The affected area is the leg. The photograph is a close-up of the affected area.
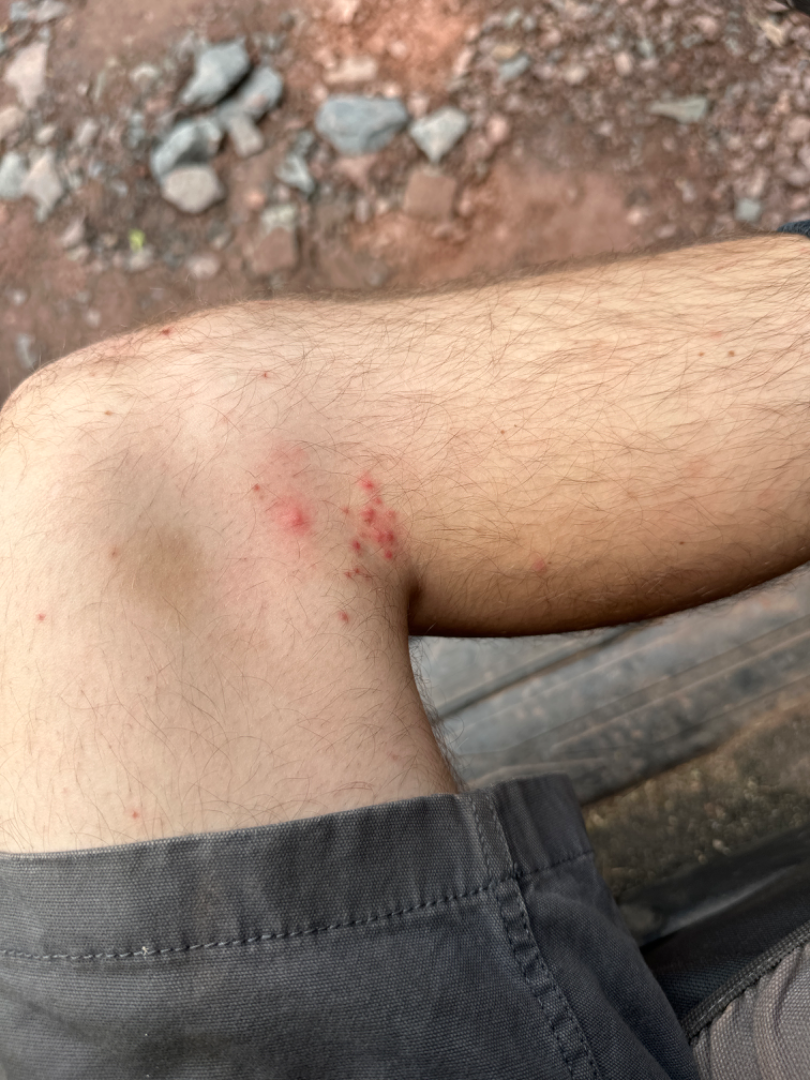Q: Could the case be diagnosed?
A: not assessable
Q: What is the lesion texture?
A: raised or bumpy
Q: How does the patient describe it?
A: a rash
Q: Duration?
A: about one day